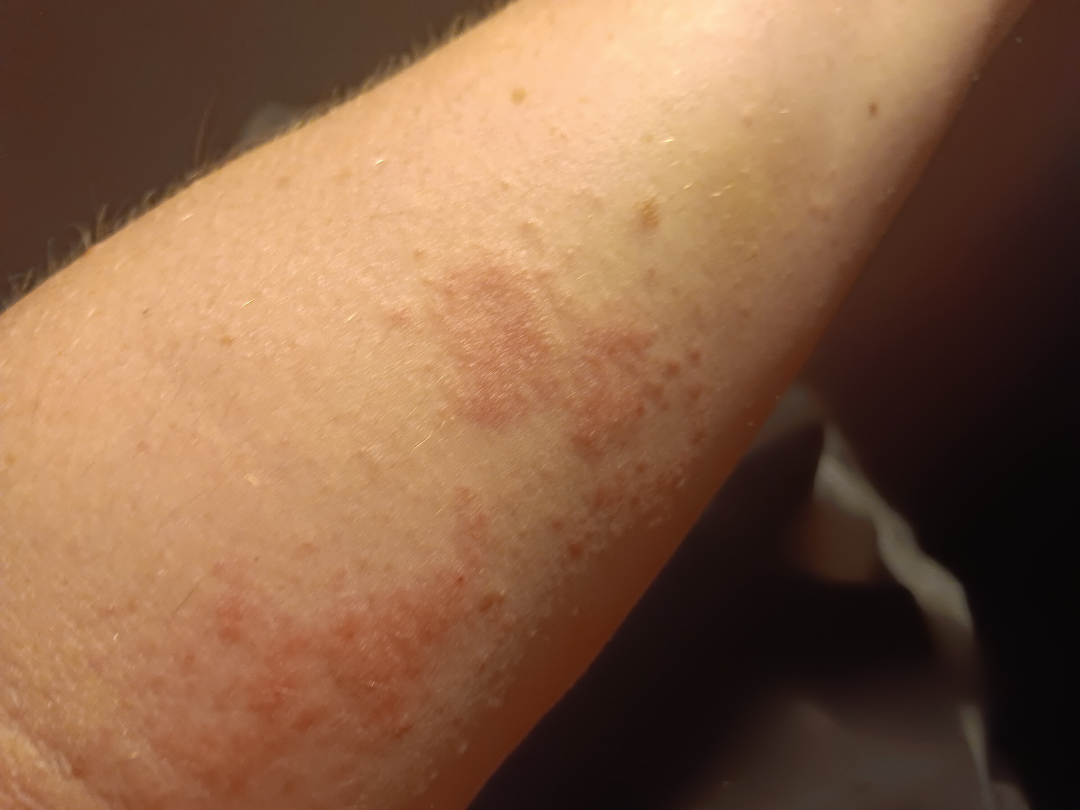Assessment:
The condition could not be reliably identified from the image.
Clinical context:
Symptoms reported: enlargement and itching. Located on the arm. The patient considered this a rash. No associated systemic symptoms reported. The photograph was taken at an angle. Texture is reported as raised or bumpy. Skin tone: Fitzpatrick II; non-clinician graders estimated Monk Skin Tone 3 or 4.